Referred with a clinical suspicion of basal cell carcinoma: 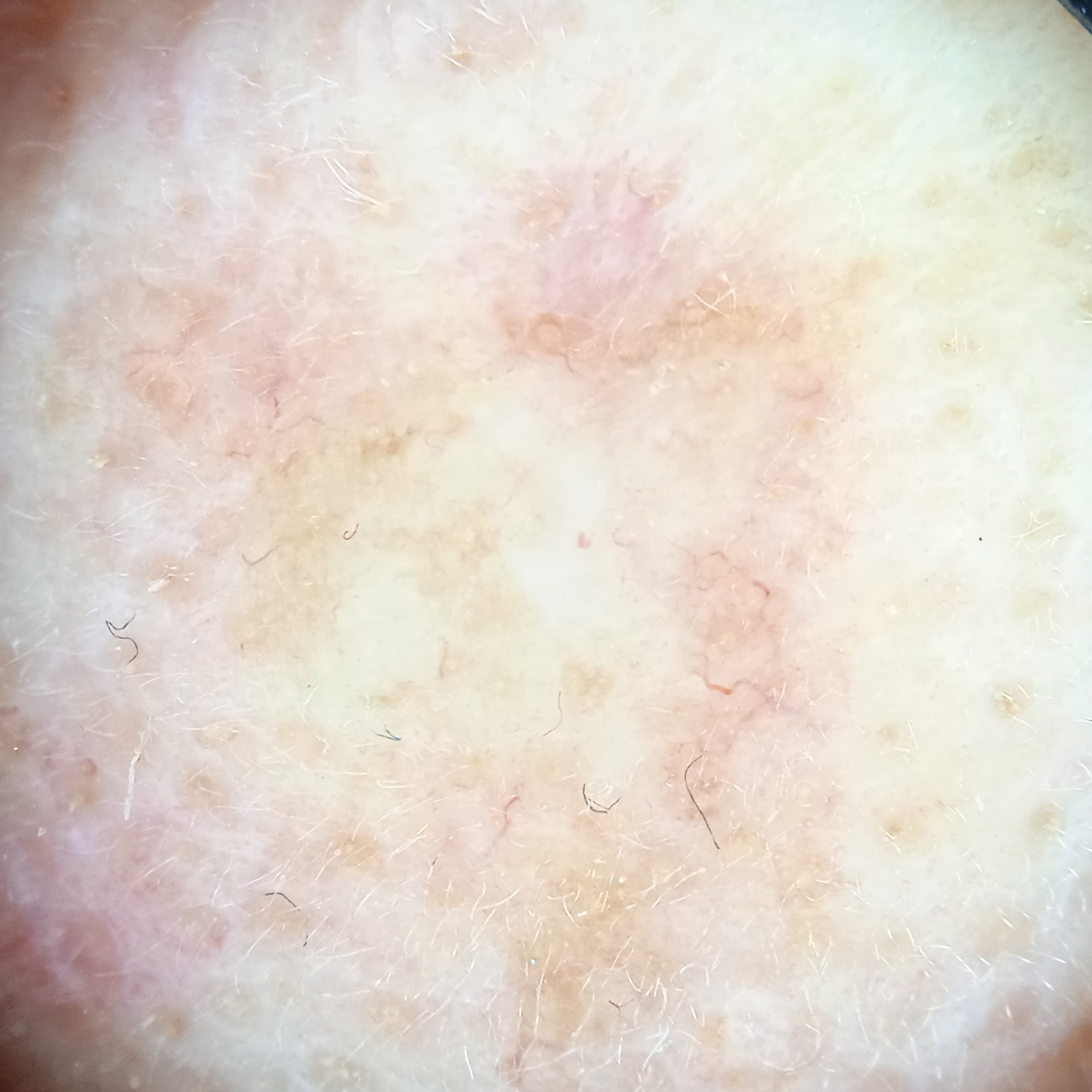Case:
• location: the face
• pathology: basal cell carcinoma (biopsy-proven)